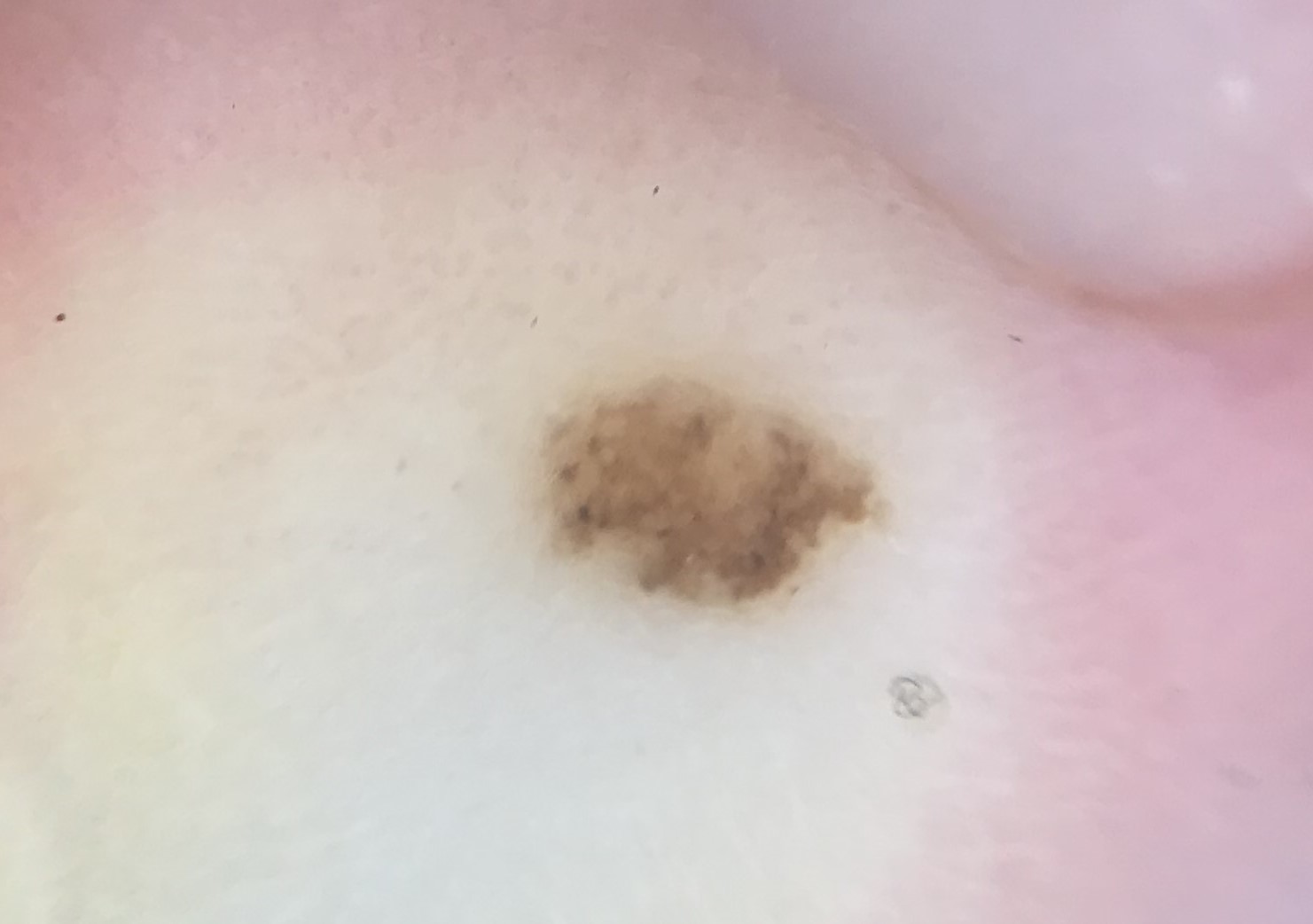category = banal
diagnostic label = acral compound nevus (expert consensus)